A clinical photograph showing a skin lesion. A patient in their 70s:
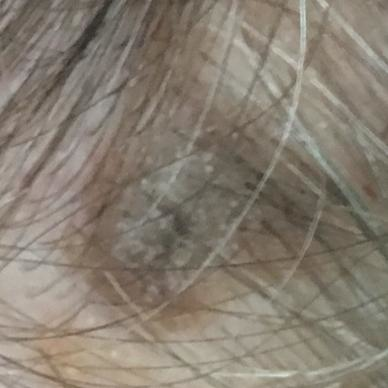Findings:
Located on the face. The patient reports that the lesion is elevated and has grown.
Conclusion:
The clinical impression was a seborrheic keratosis.